The lesion is described as fluid-filled and raised or bumpy · the lesion involves the back of the torso, arm, head or neck and back of the hand · the photograph was taken at an angle · the condition has been present for more than one year · associated systemic symptoms include fatigue, shortness of breath, chills, joint pain and mouth sores · the subject is a female aged 30–39 · the lesion is associated with darkening, itching, pain, burning and bothersome appearance — 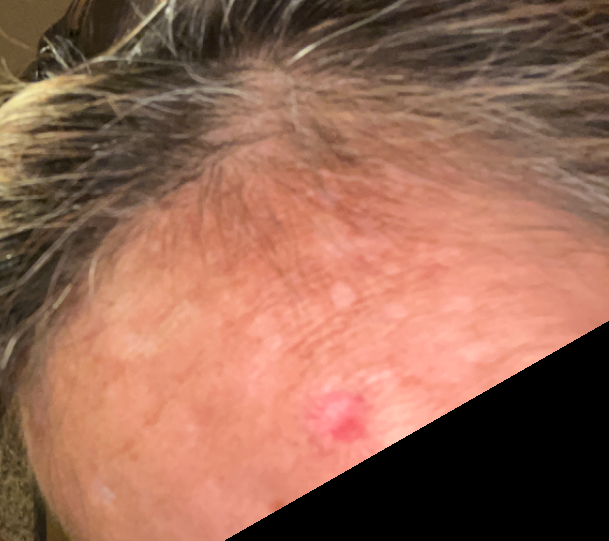On dermatologist assessment of the image, Basal Cell Carcinoma (67%); Traumatic ulcer (33%).